A female subject, in their mid-60s. A dermoscopic image of a skin lesion.
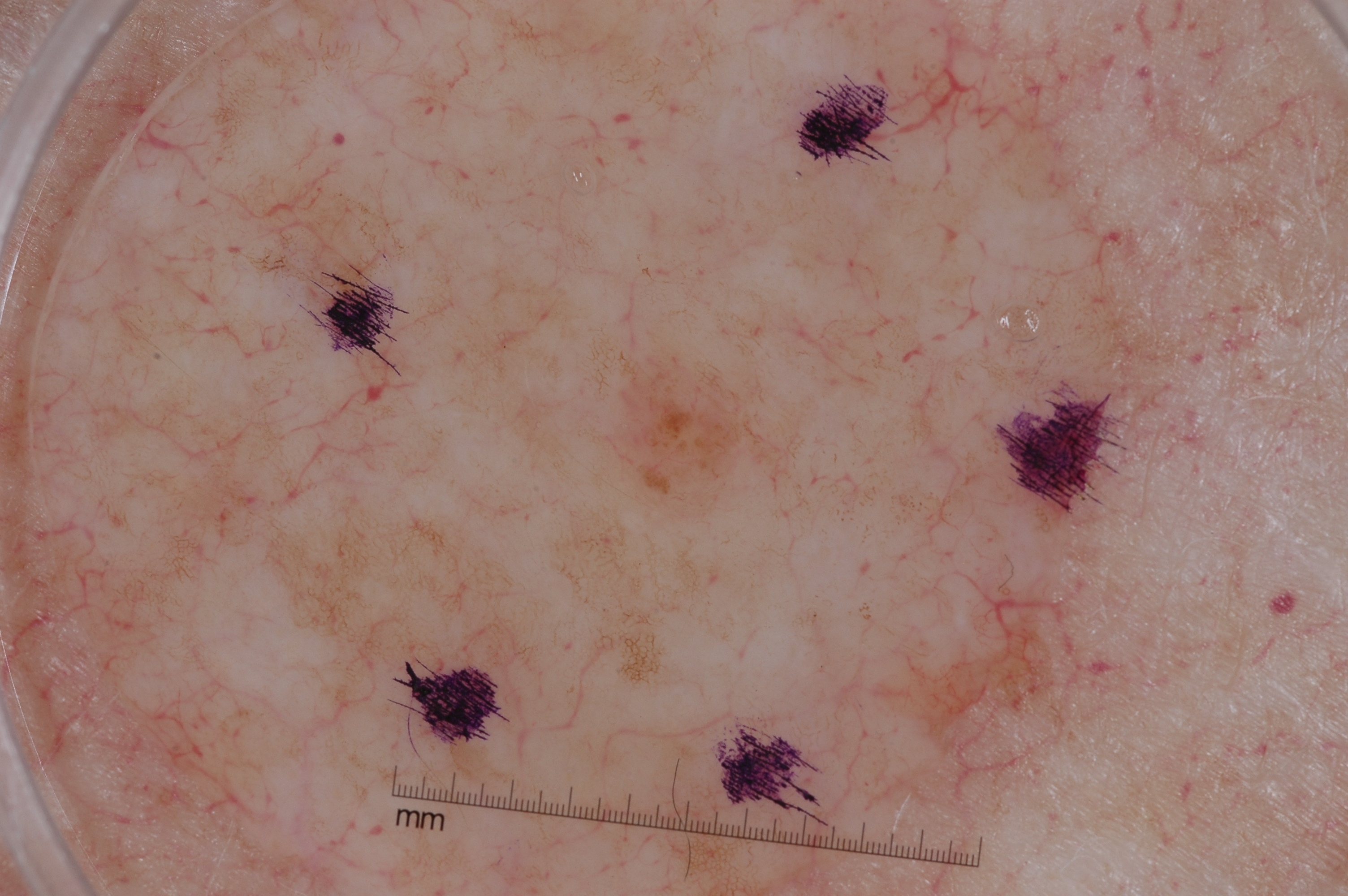size = small; absent dermoscopic findings = negative network, streaks, pigment network, and milia-like cysts; lesion bbox = <bbox>633, 371, 747, 483</bbox>; impression = a melanocytic nevus.